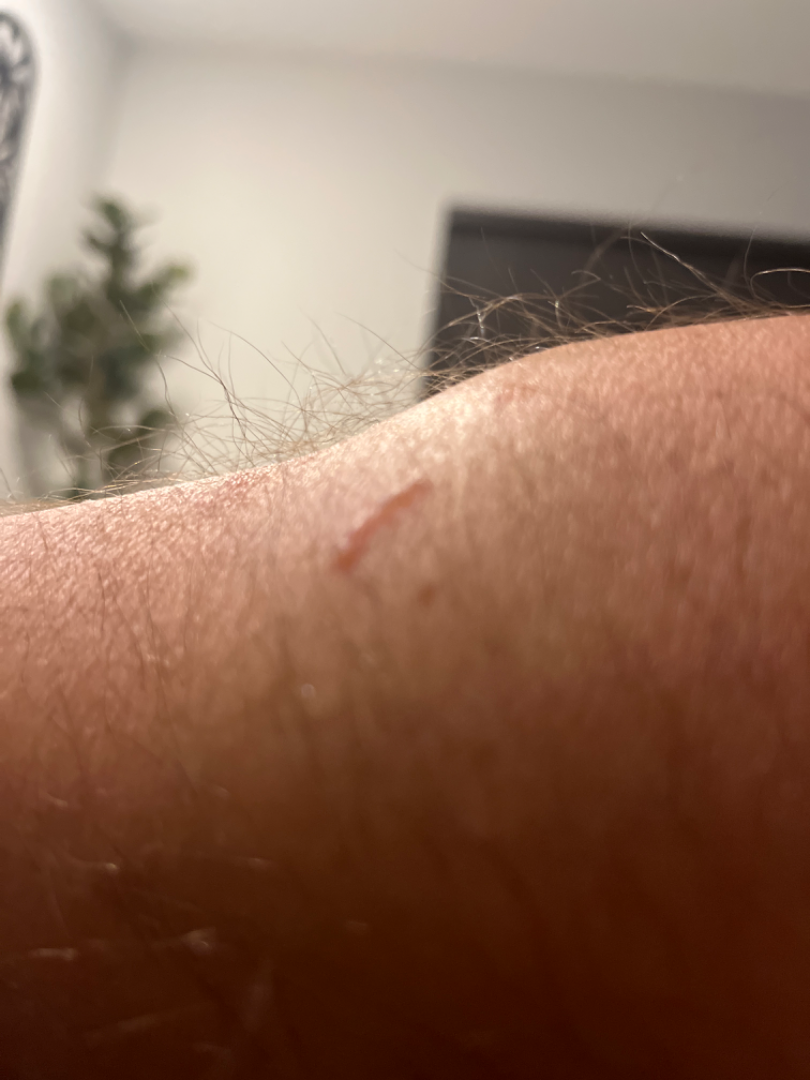patient=male, age 18–29; symptom duration=one to four weeks; self-categorized as=a rash; other reported symptoms=none reported; described texture=raised or bumpy and fluid-filled; location=arm and leg; framing=at an angle; clinical impression=in keeping with Contact dermatitis caused by Rhus diversiloba.